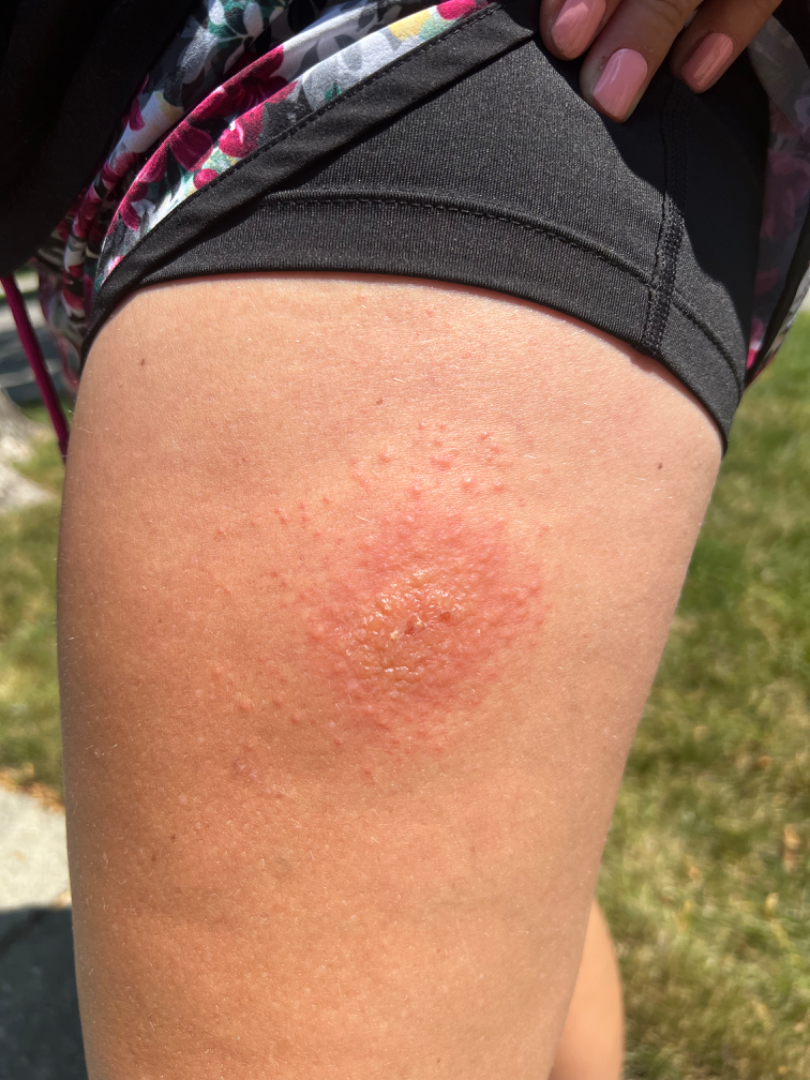Q: What is the differential diagnosis?
A: Allergic Contact Dermatitis (considered); Herpes Simplex (considered); Skin and soft tissue atypical mycobacterial infection (lower probability)